Fitzpatrick phototype II. A female subject aged 18-22. A dermatoscopic image of a skin lesion — 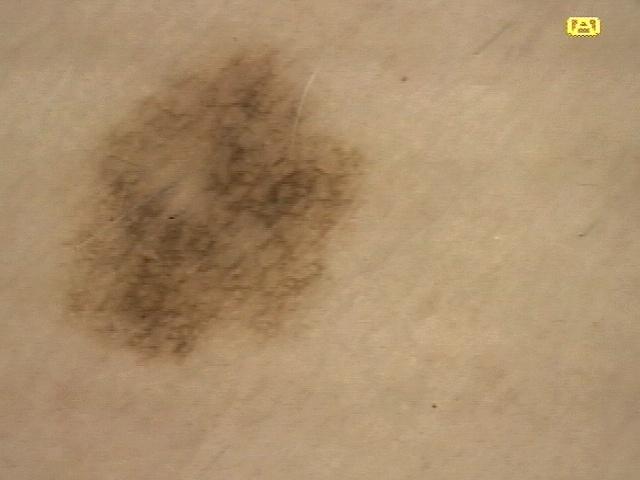anatomic site: the trunk, specifically the posterior trunk; impression: Nevus.